An image taken at a distance. The affected area is the leg, front of the torso and arm. The patient is 30–39, female:
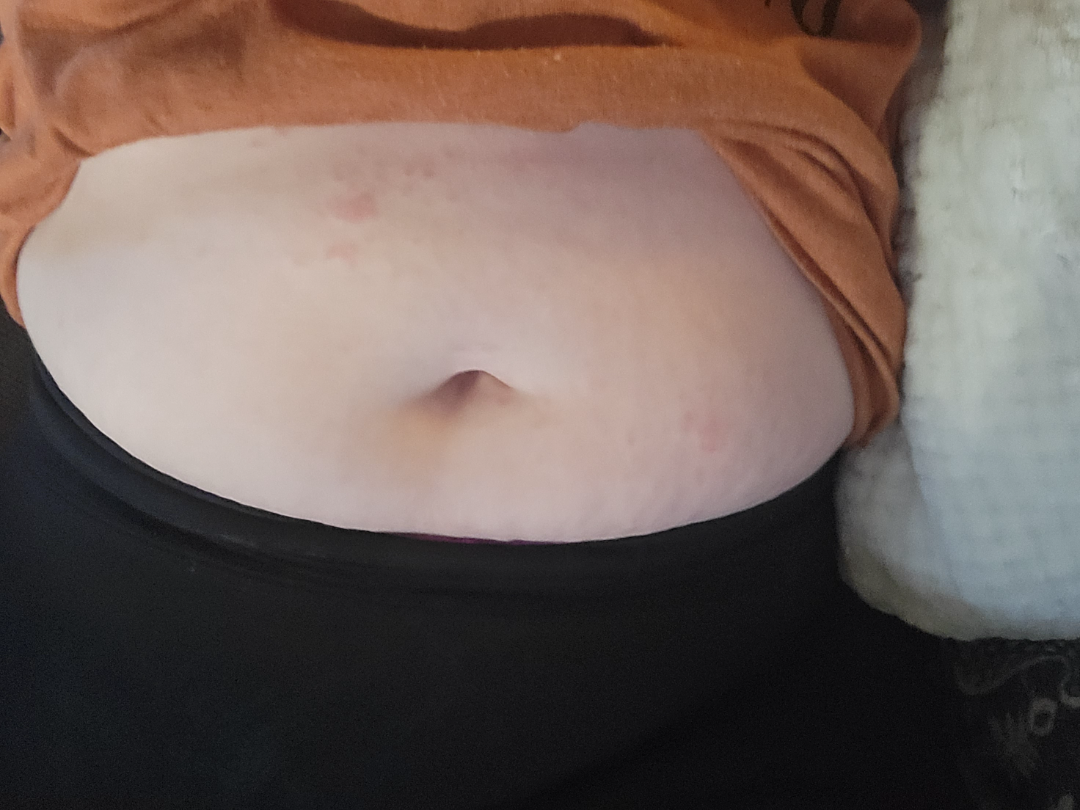Assessment:
Diagnostic features were not clearly distinguishable in this photograph.